A dermatoscopic image of a skin lesion: 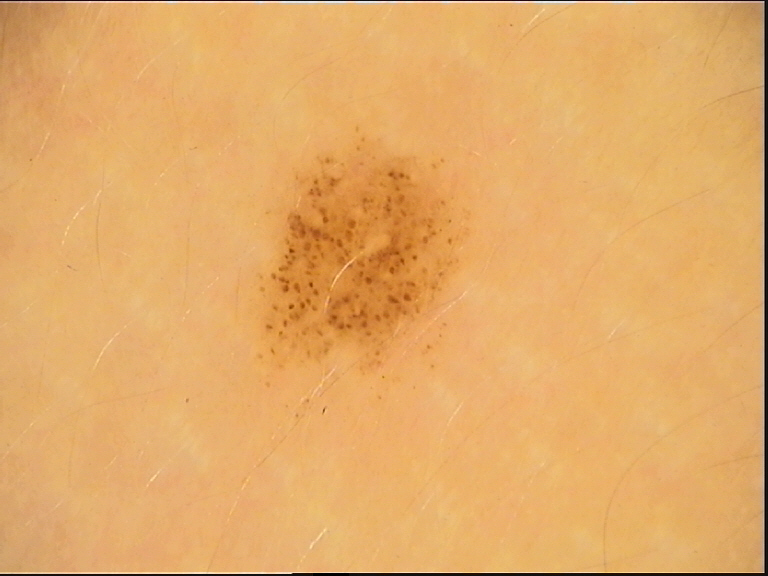Findings: The architecture is that of a banal lesion. Conclusion: Consistent with a junctional nevus.